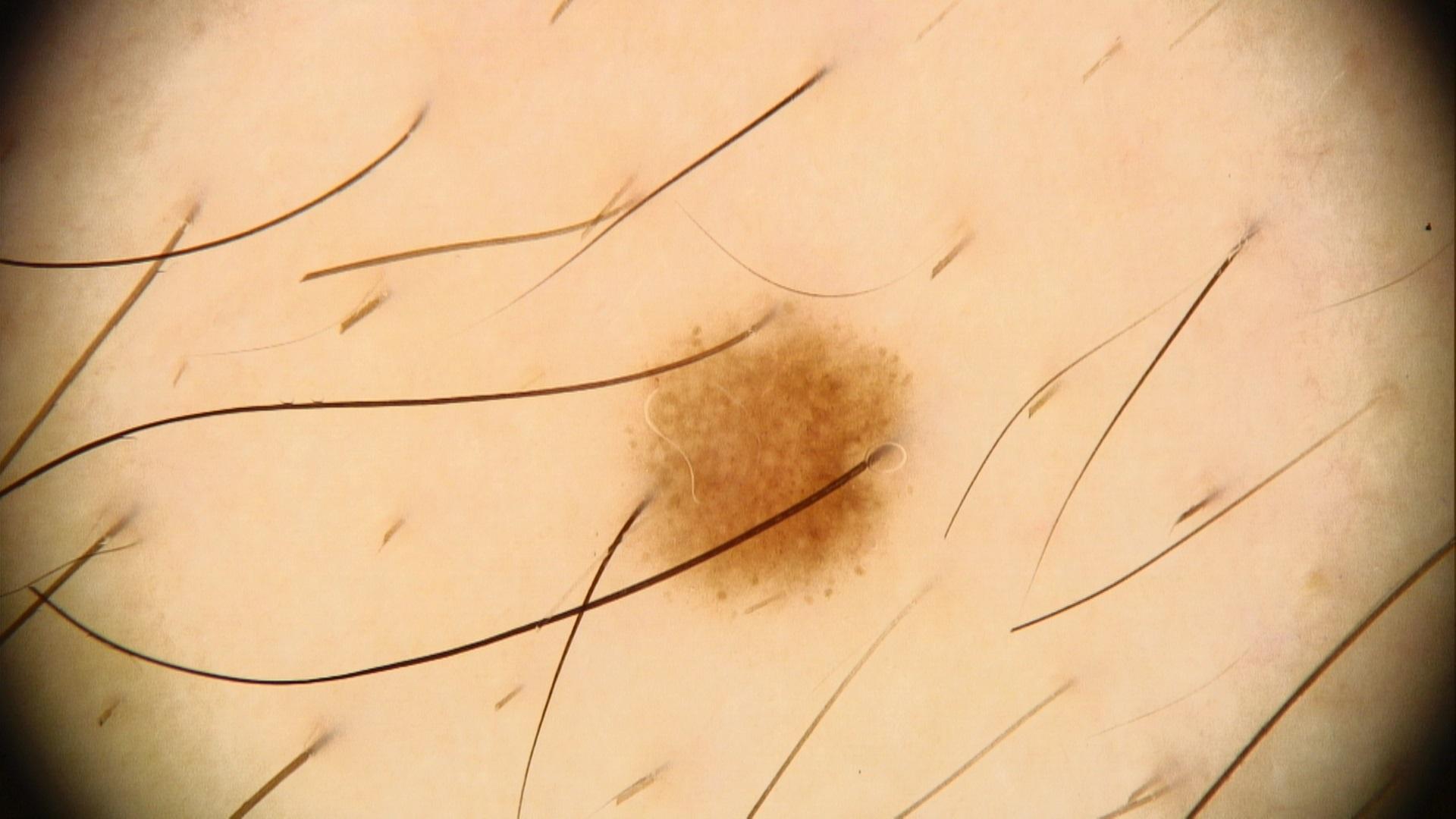  patient:
    age_approx: 20
    sex: male
  image: dermoscopy
  lesion_location:
    region: the trunk
  diagnosis:
    name: Nevus
    malignancy: benign
    confirmation: expert clinical impression
    lineage: melanocytic